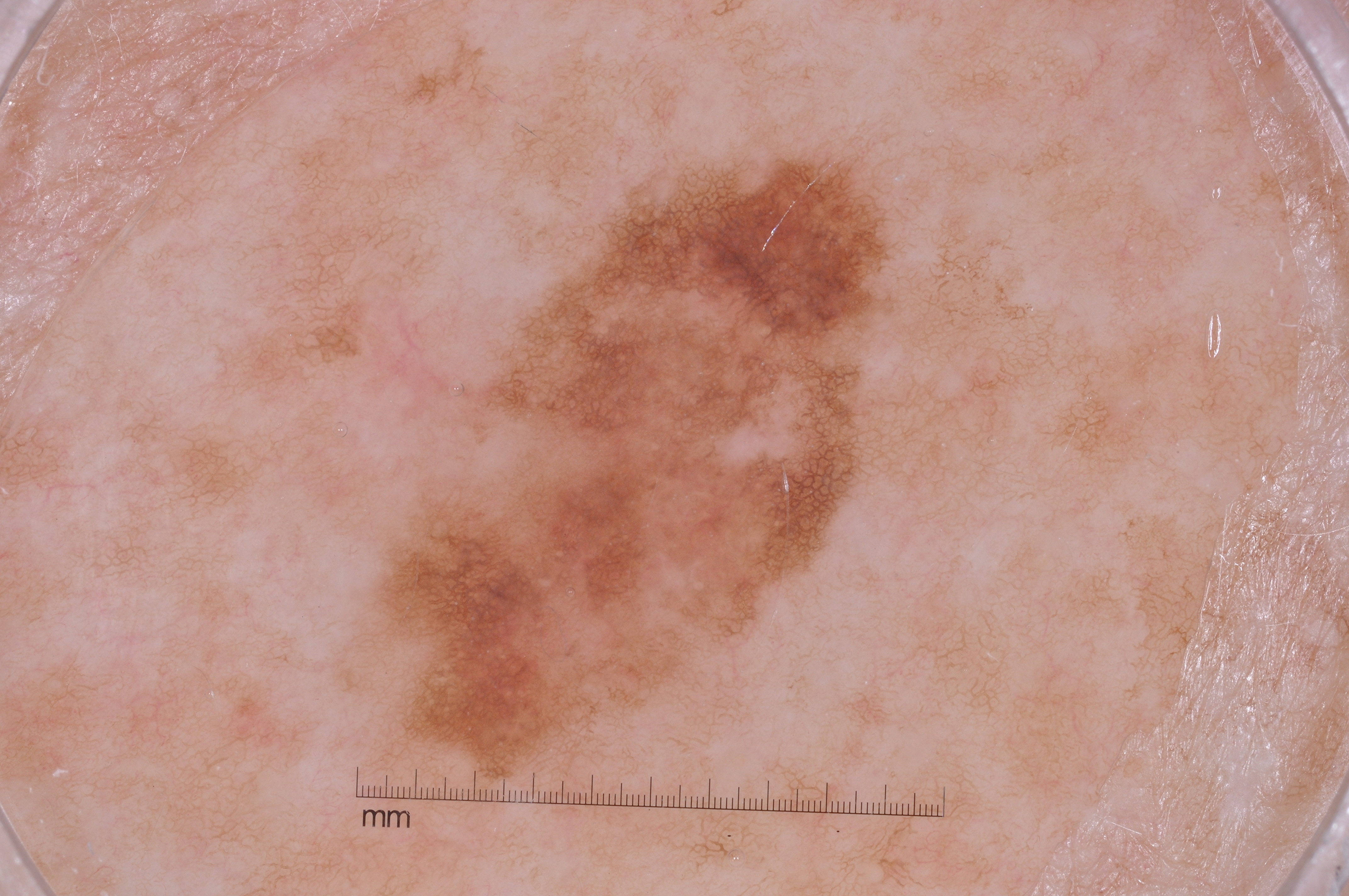{
  "image": {
    "modality": "dermoscopy"
  },
  "patient": {
    "sex": "female",
    "age_approx": 60
  },
  "lesion_location": {
    "bbox_xyxy": [
      314,
      147,
      918,
      820
    ]
  },
  "dermoscopic_features": {
    "present": [
      "pigment network"
    ],
    "absent": [
      "milia-like cysts",
      "negative network",
      "streaks"
    ]
  },
  "diagnosis": {
    "name": "melanoma",
    "malignancy": "malignant",
    "lineage": "melanocytic",
    "provenance": "histopathology"
  }
}